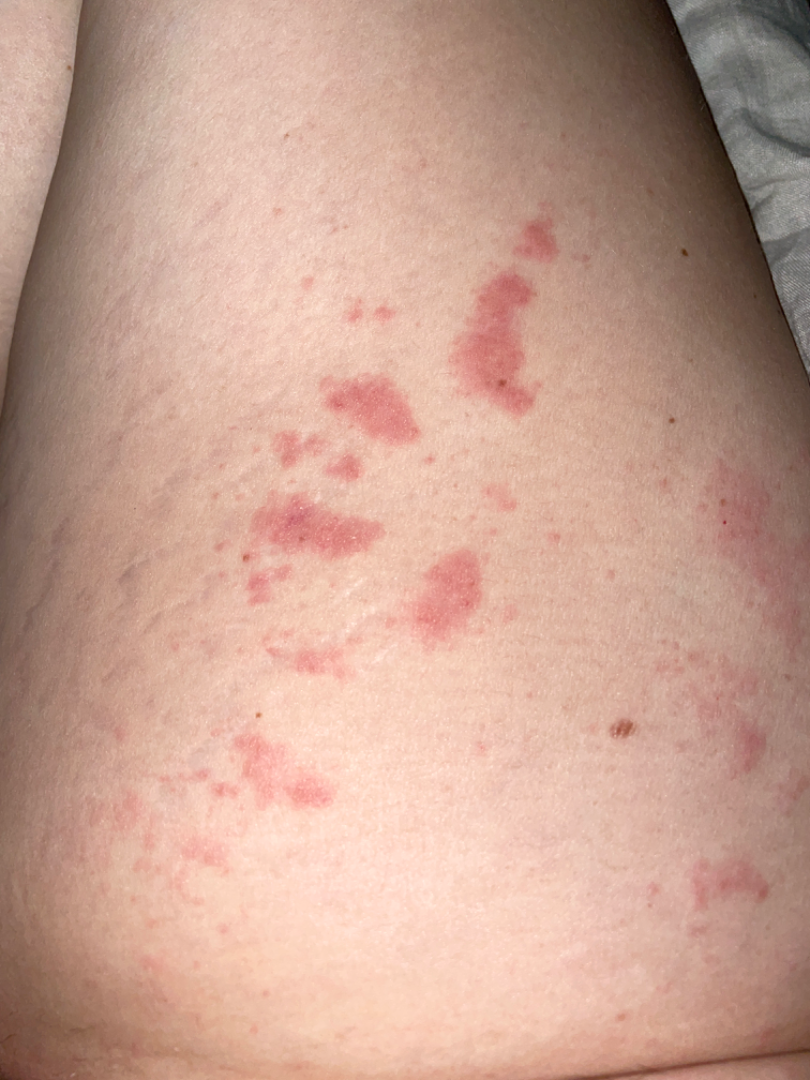The reviewer was unable to grade this case for skin condition.